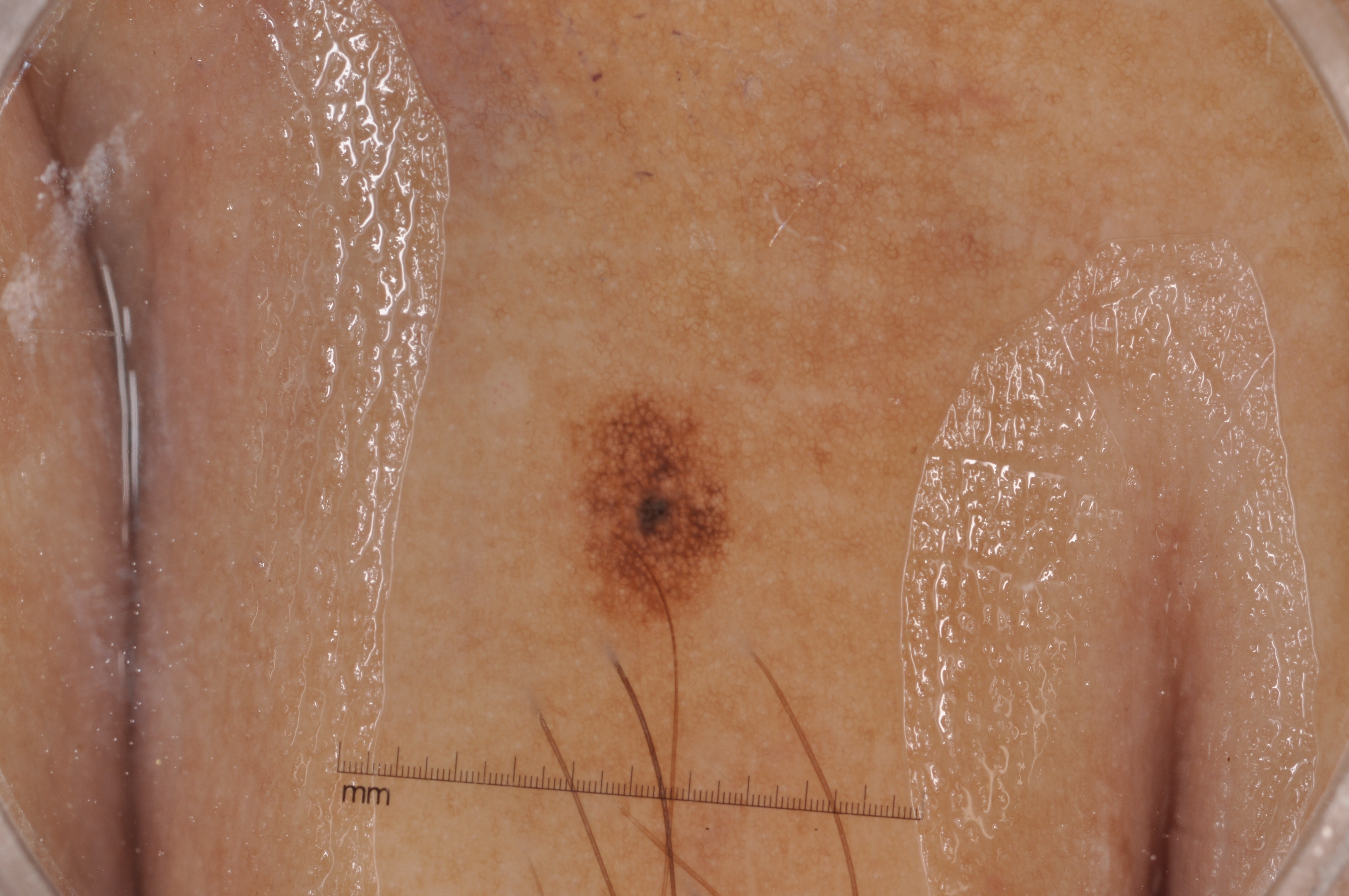A skin lesion imaged with a dermatoscope.
A male subject, aged 73-77.
The dermoscopic pattern shows pigment network.
The lesion takes up about 4% of the image.
The lesion spans [546,370,744,639].
The lesion was assessed as a melanocytic nevus.